A dermoscopic photograph of a skin lesion: 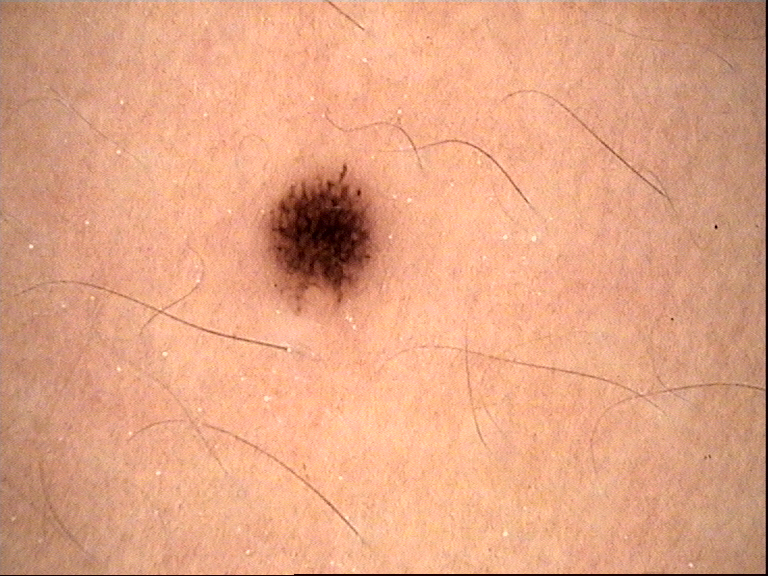Conclusion:
Diagnosed as a dysplastic junctional nevus.